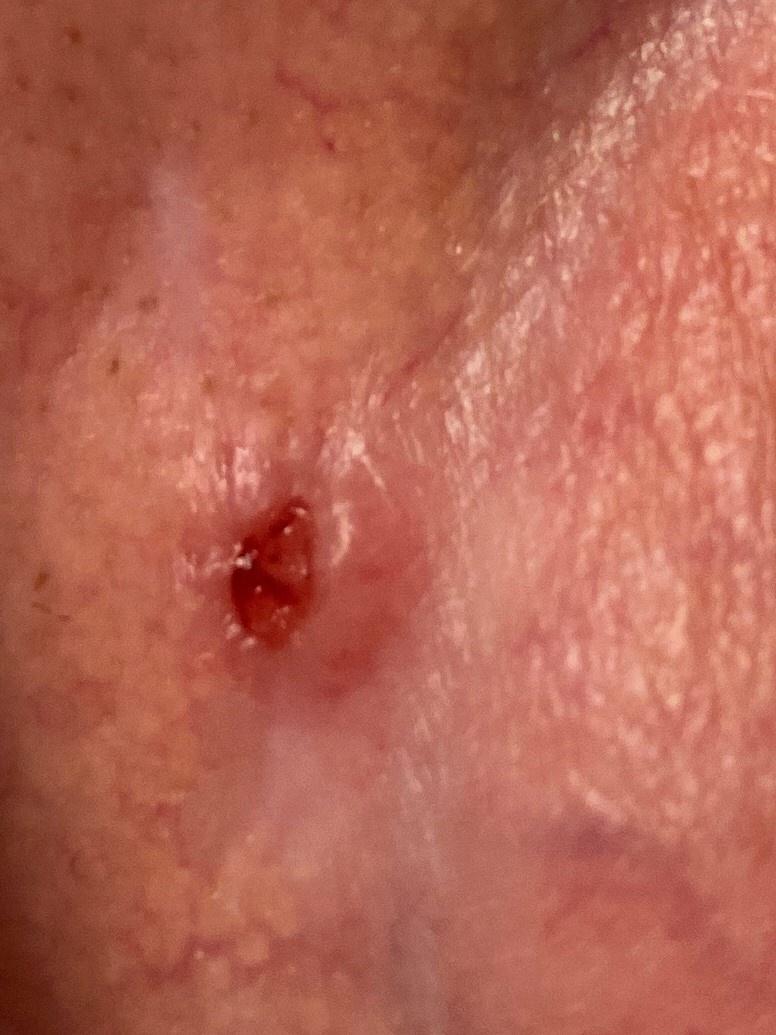Image and clinical context: A male patient about 80 years old. The chart documents a previous melanoma but no melanoma in first-degree relatives. Recorded as skin type I. The lesion was found on the head or neck. Pathology: Biopsy-confirmed as a malignant, adnexal lesion — a basal cell carcinoma.